The photograph is a close-up of the affected area, the subject is female.
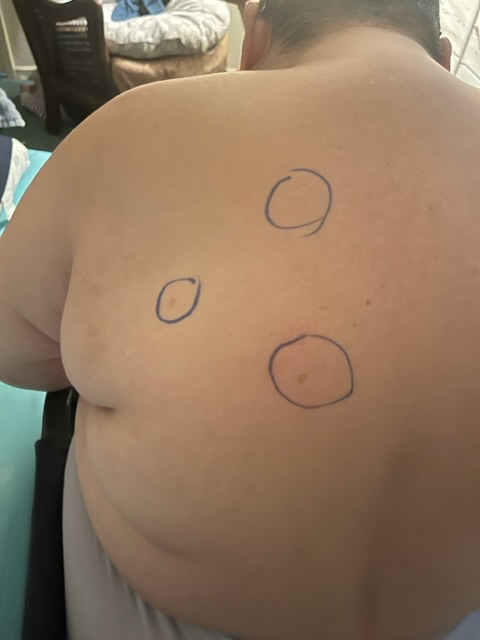assessment: indeterminate